The subject is 50–59, female; the photograph was taken at an angle; the lesion involves the palm — 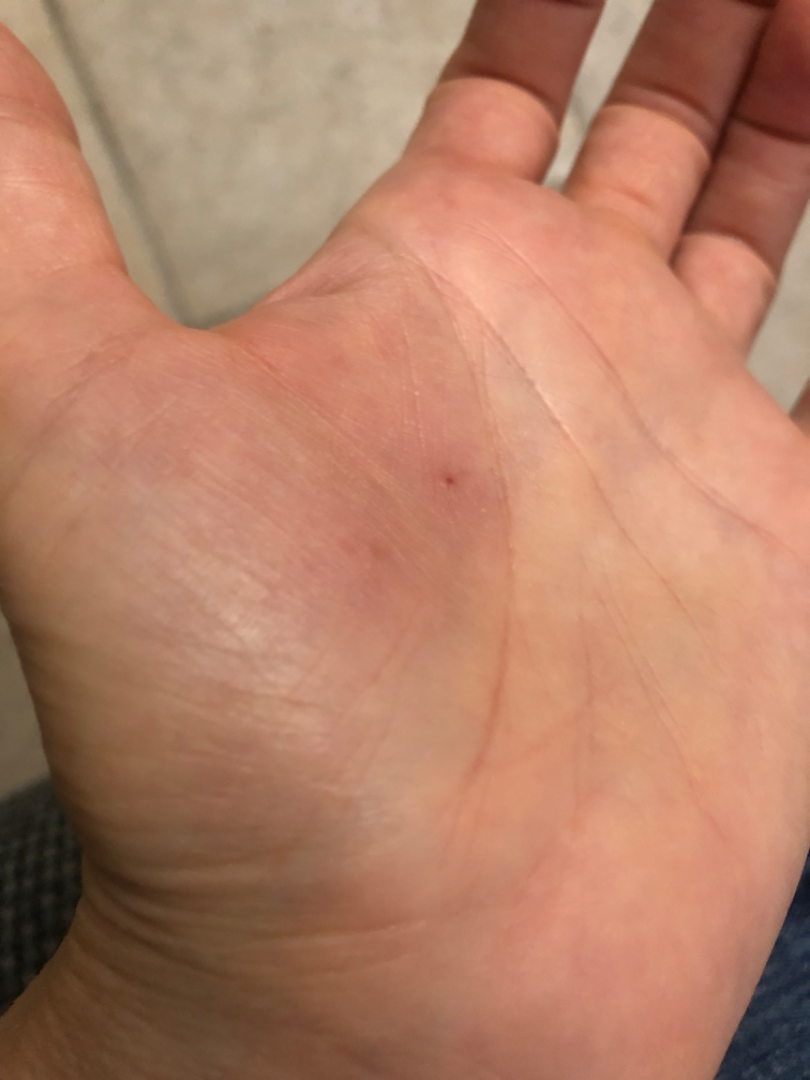Review: On remote dermatologist review: most consistent with Eczema.